A dermoscopic close-up of a skin lesion.
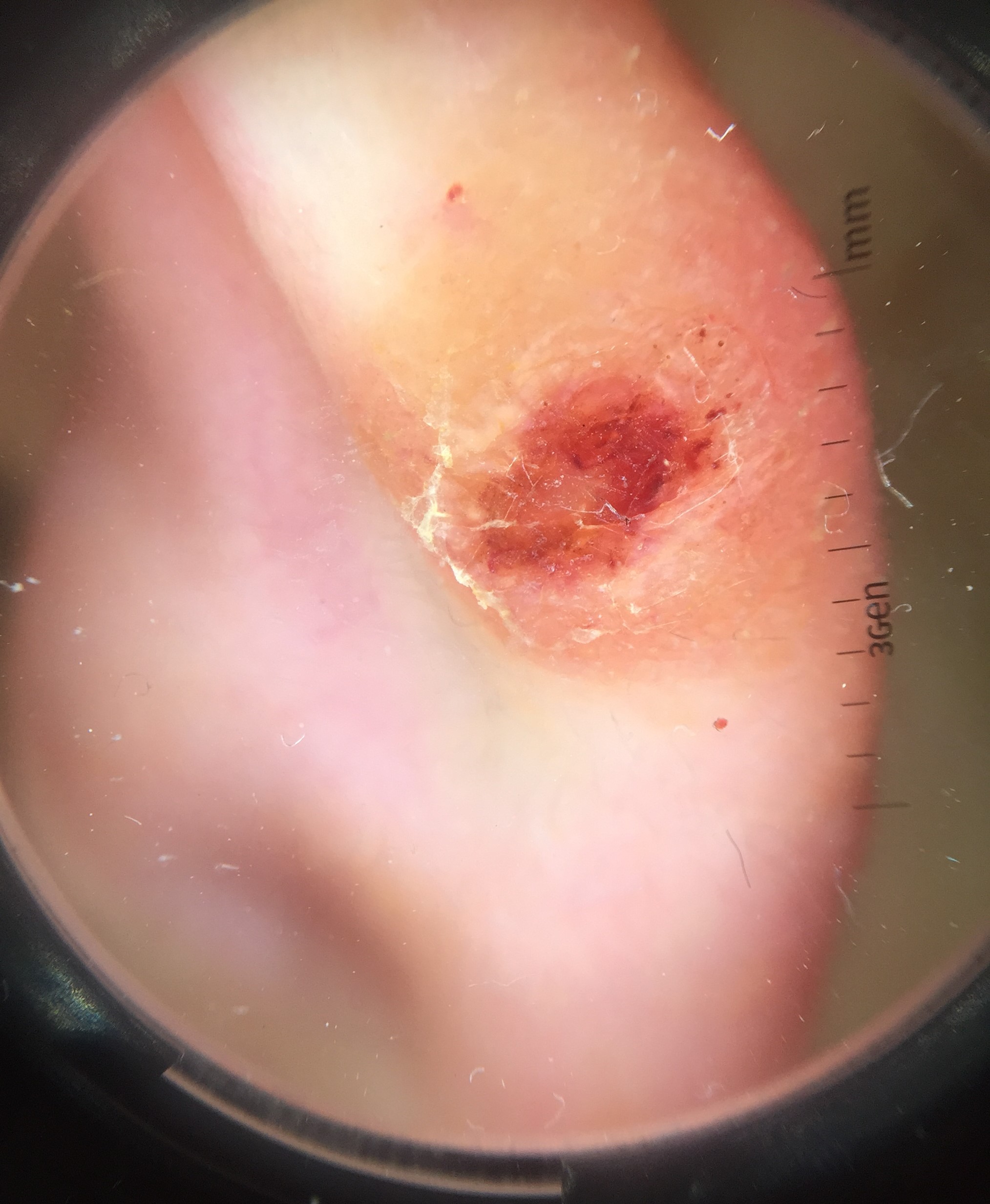subtype — keratinocytic
diagnostic label — squamous cell carcinoma (biopsy-proven)